The photograph was taken at a distance, the affected area is the leg, the patient is female.
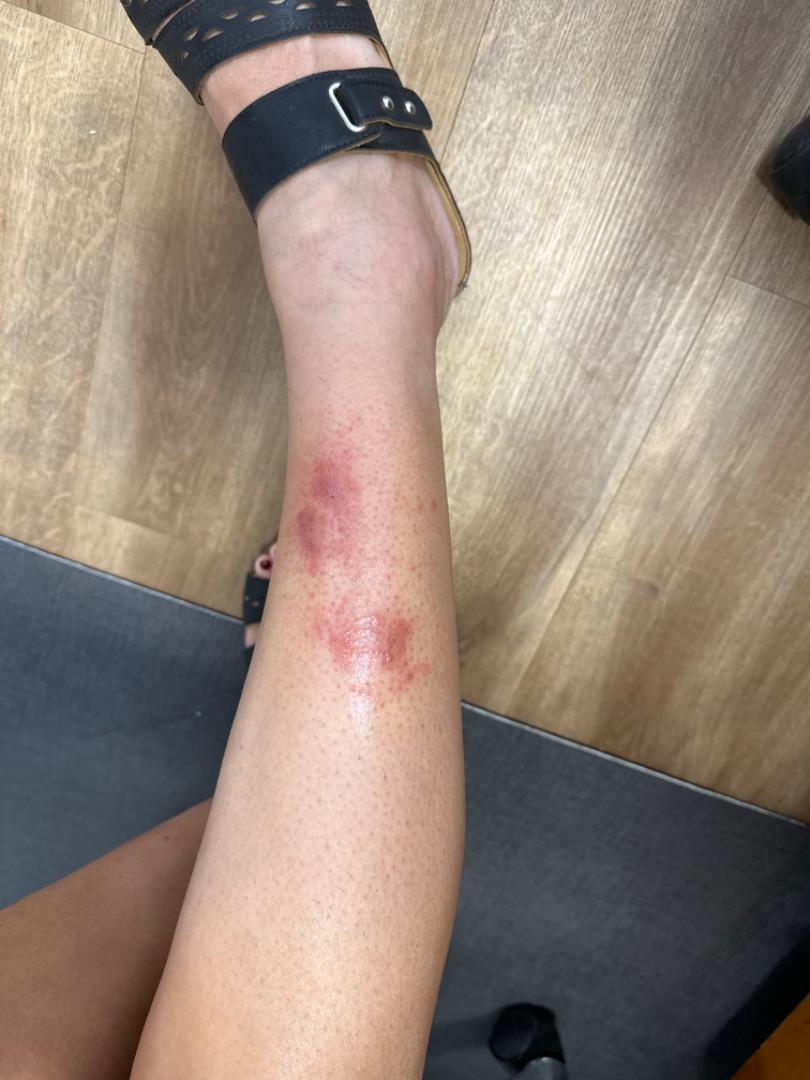The case was indeterminate on photographic review.
The patient described the issue as skin that appeared healthy to them.
Texture is reported as raised or bumpy.
No constitutional symptoms were reported.
The patient indicates the condition has been present for less than one week.
Skin tone: Fitzpatrick skin type II; human graders estimated MST 2–3.